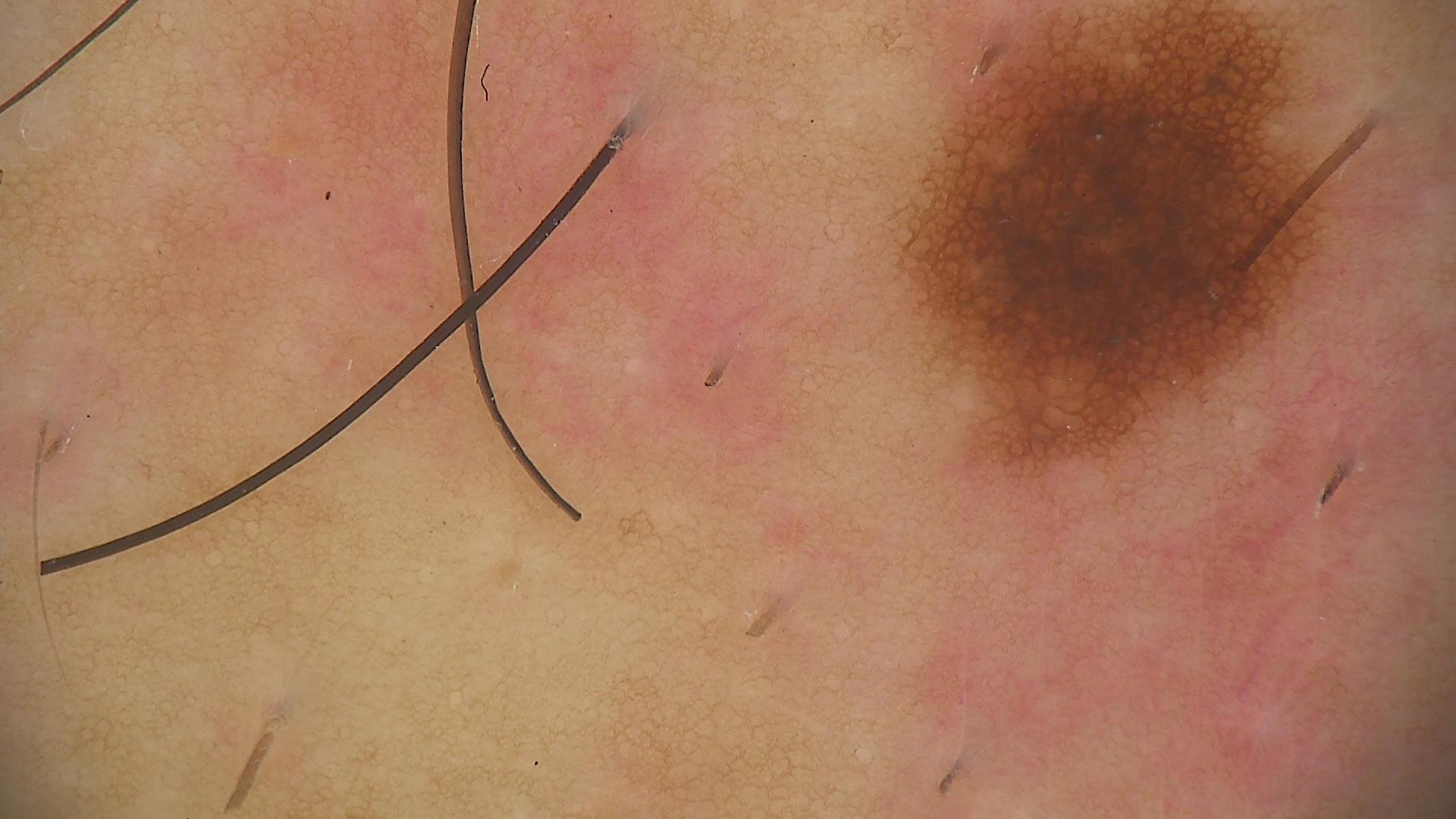diagnostic label: dysplastic junctional nevus (expert consensus)